The lesion involves the leg and top or side of the foot, this image was taken at a distance, the contributor is a male aged 30–39 — 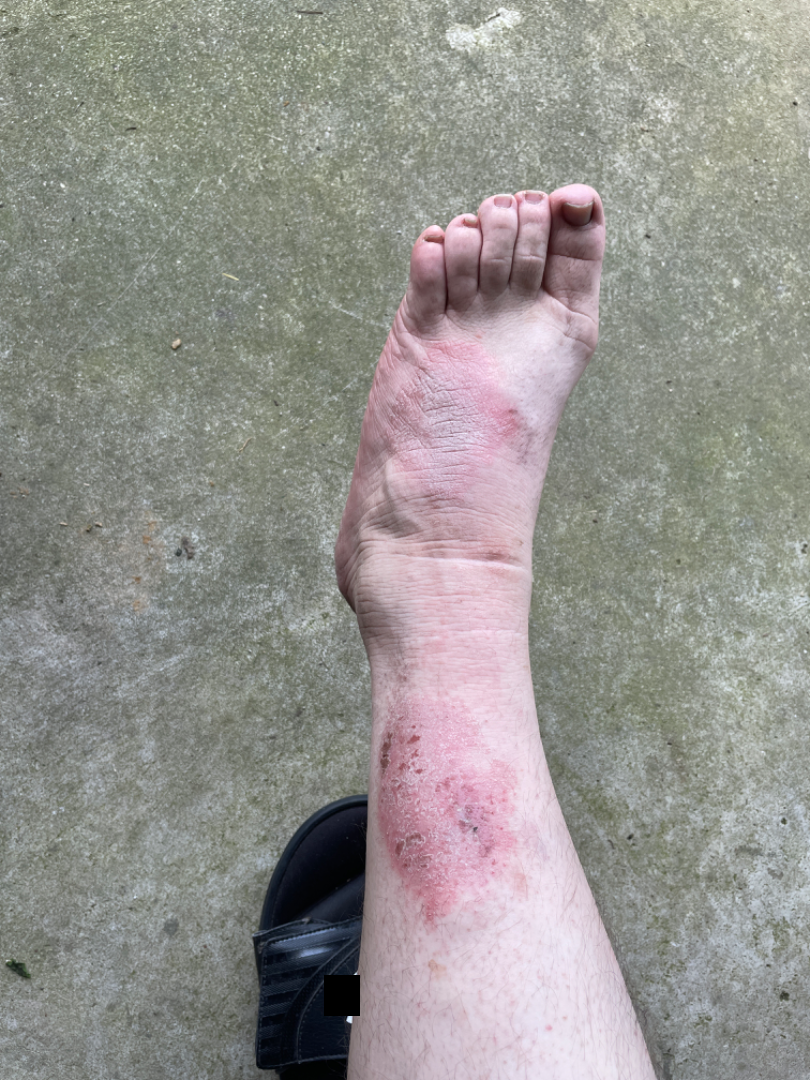assessment: Eczema, Impetigo and Allergic Contact Dermatitis were considered with similar weight.